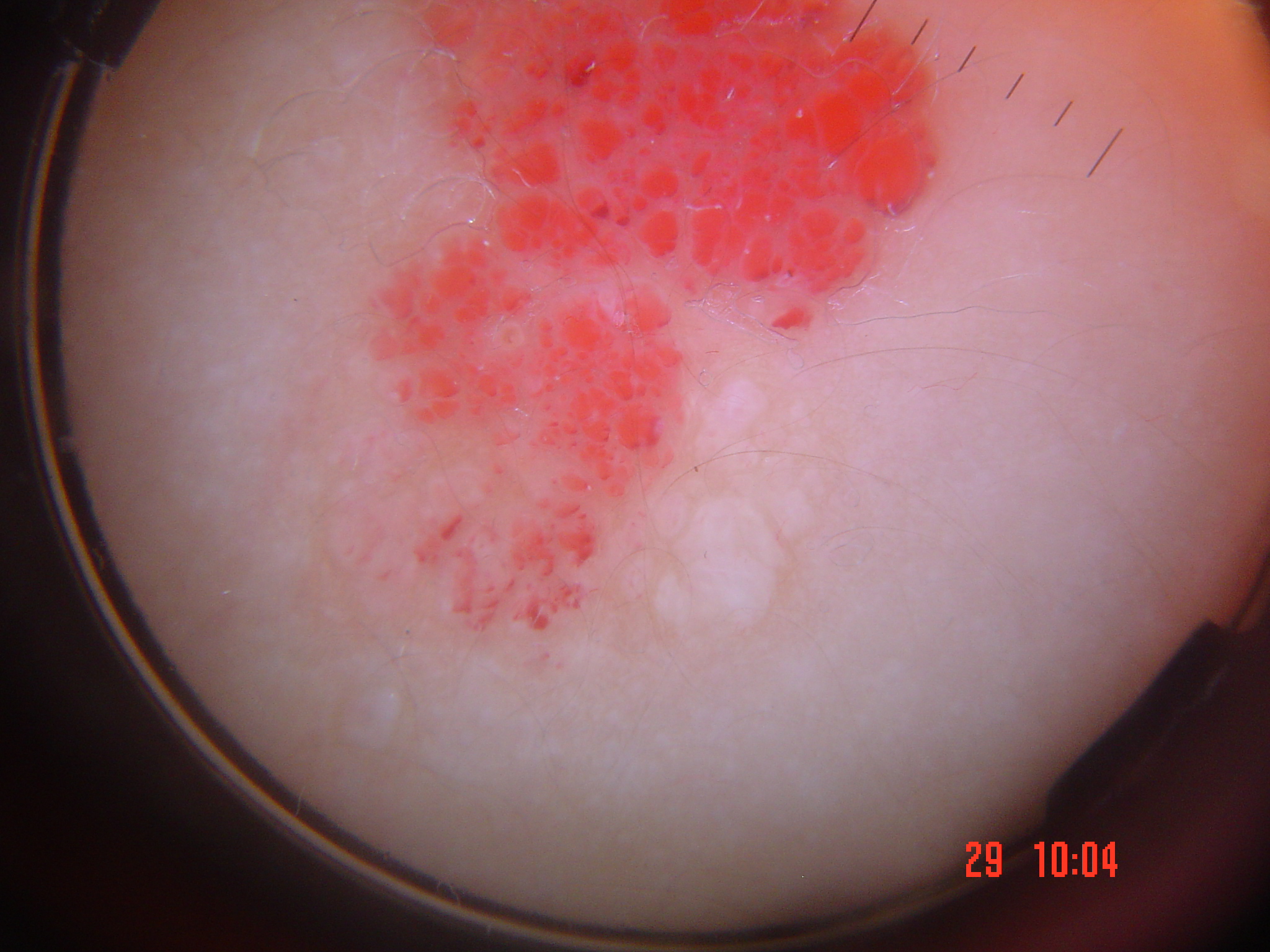Impression:
Labeled as a lymphangioma.